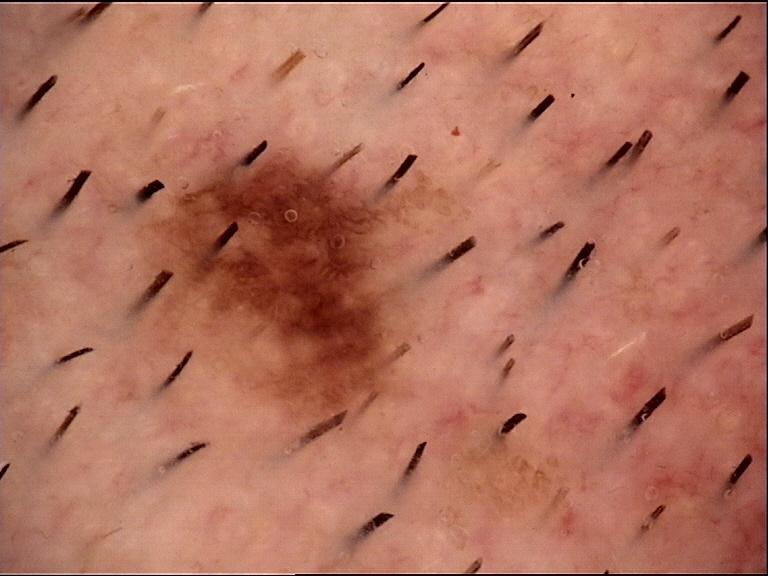Classified as a dysplastic junctional nevus.